Dermoscopy of a skin lesion:
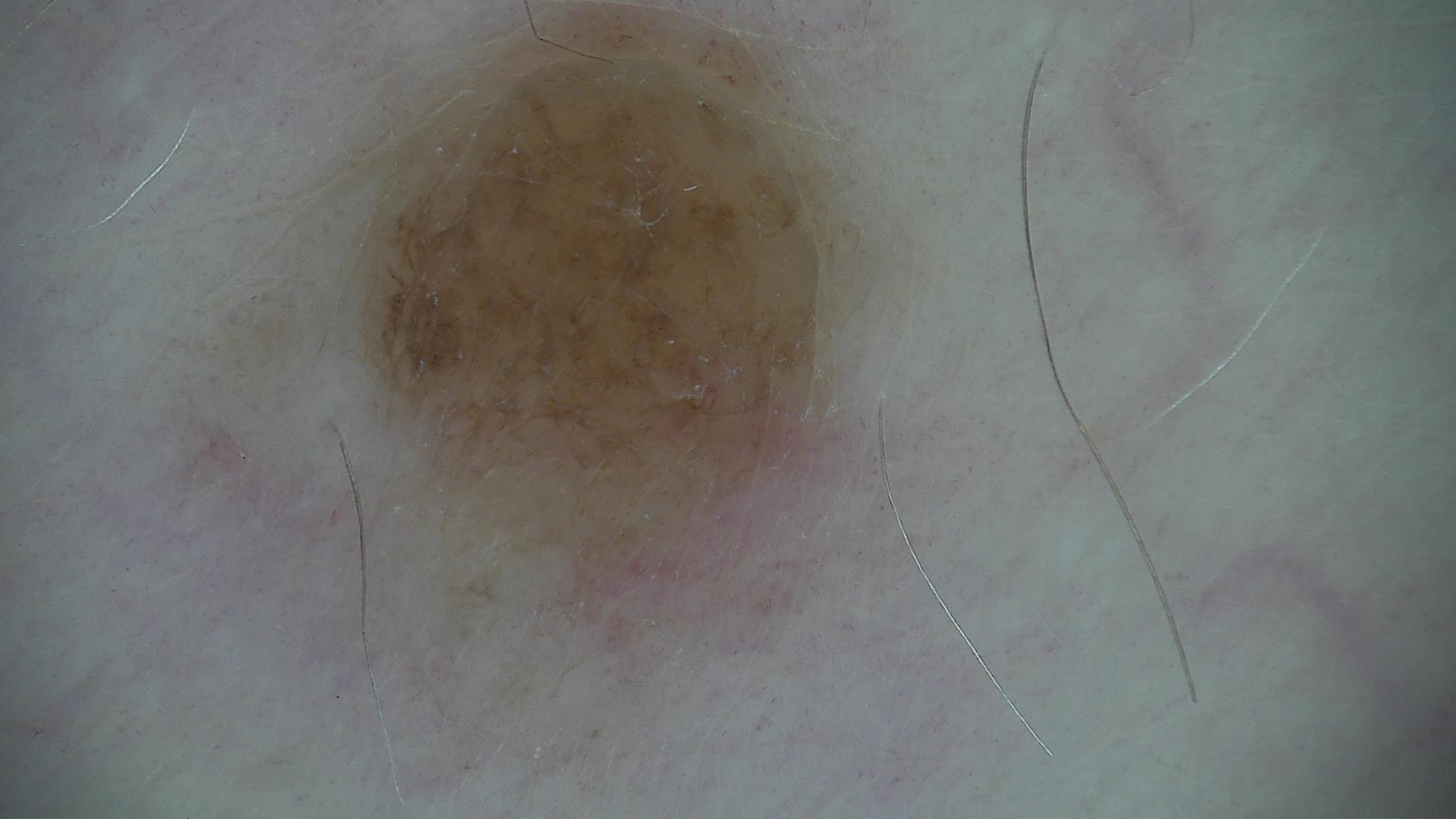diagnosis = dermal nevus (expert consensus).